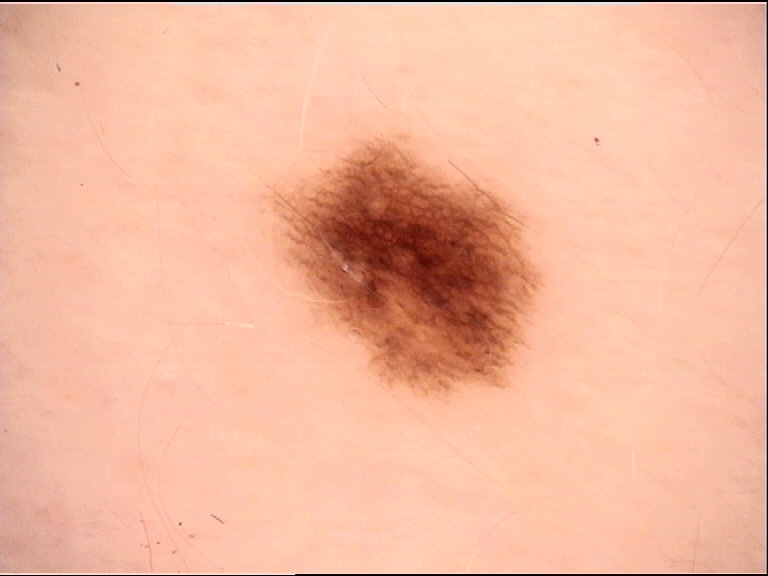image = dermatoscopy | label = dysplastic junctional nevus (expert consensus).